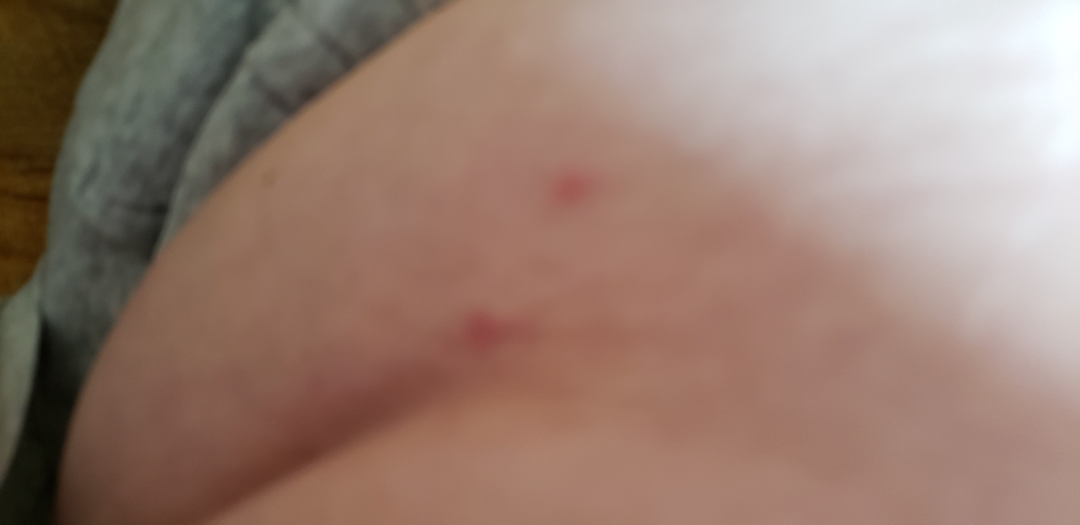{
  "assessment": "unable to determine"
}